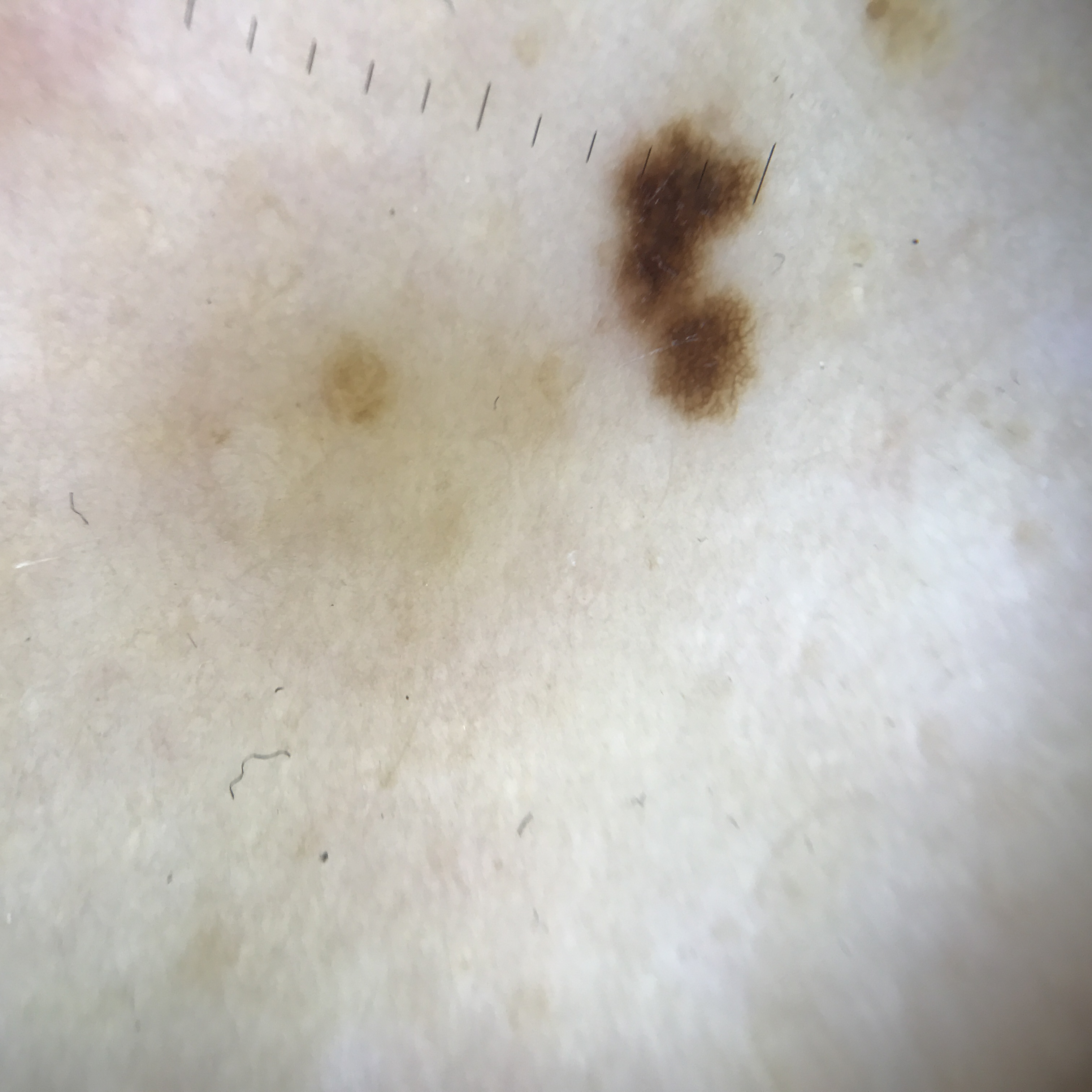diagnostic label: dysplastic junctional nevus (expert consensus).